Fitzpatrick skin type II; a smartphone photograph of a skin lesion; the chart records prior malignancy (patient or family) and prior skin cancer (patient or family).
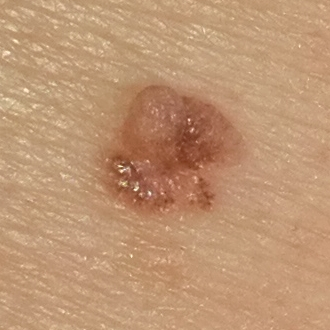<case>
<lesion_location>the back</lesion_location>
<lesion_size>
<diameter_1_mm>6.0</diameter_1_mm>
<diameter_2_mm>5.0</diameter_2_mm>
</lesion_size>
<diagnosis>
<name>basal cell carcinoma</name>
<code>BCC</code>
<malignancy>malignant</malignancy>
<confirmation>histopathology</confirmation>
</diagnosis>
</case>